Dermoscopy of a skin lesion:
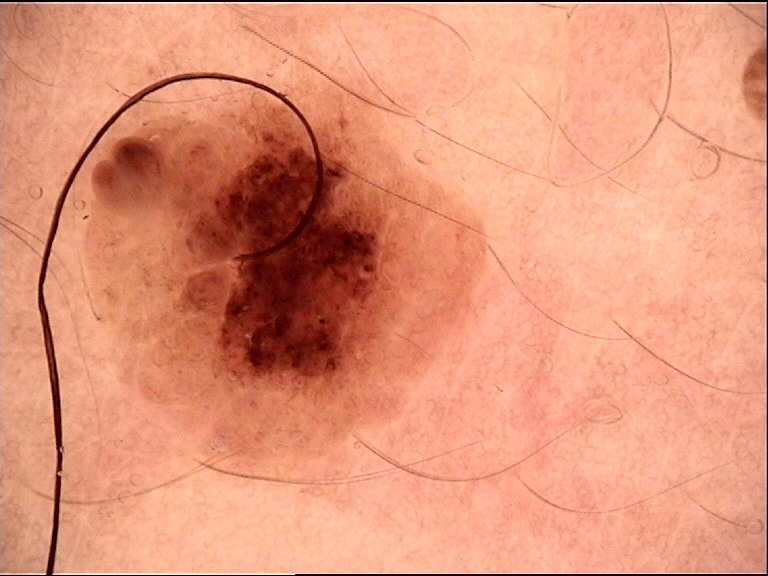Case: This is a banal lesion. Conclusion: The diagnostic label was a dermal nevus.